The affected area is the head or neck · a close-up photograph · male patient, age 50–59.
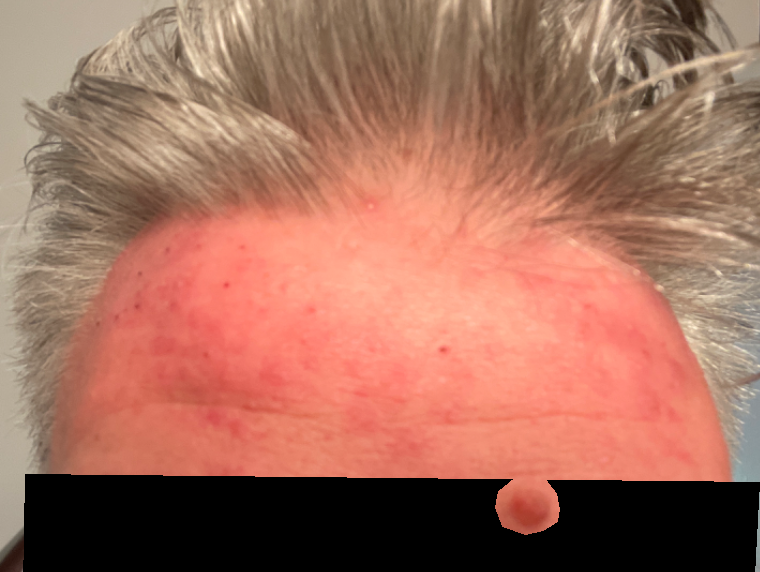{
  "texture": "rough or flaky",
  "patient_category": "a rash",
  "systemic_symptoms": "none reported",
  "symptoms": "bothersome appearance",
  "skin_tone": {
    "fitzpatrick": "II",
    "monk_skin_tone": [
      2,
      3
    ]
  },
  "differential": {
    "leading": [
      "Rosacea"
    ]
  }
}